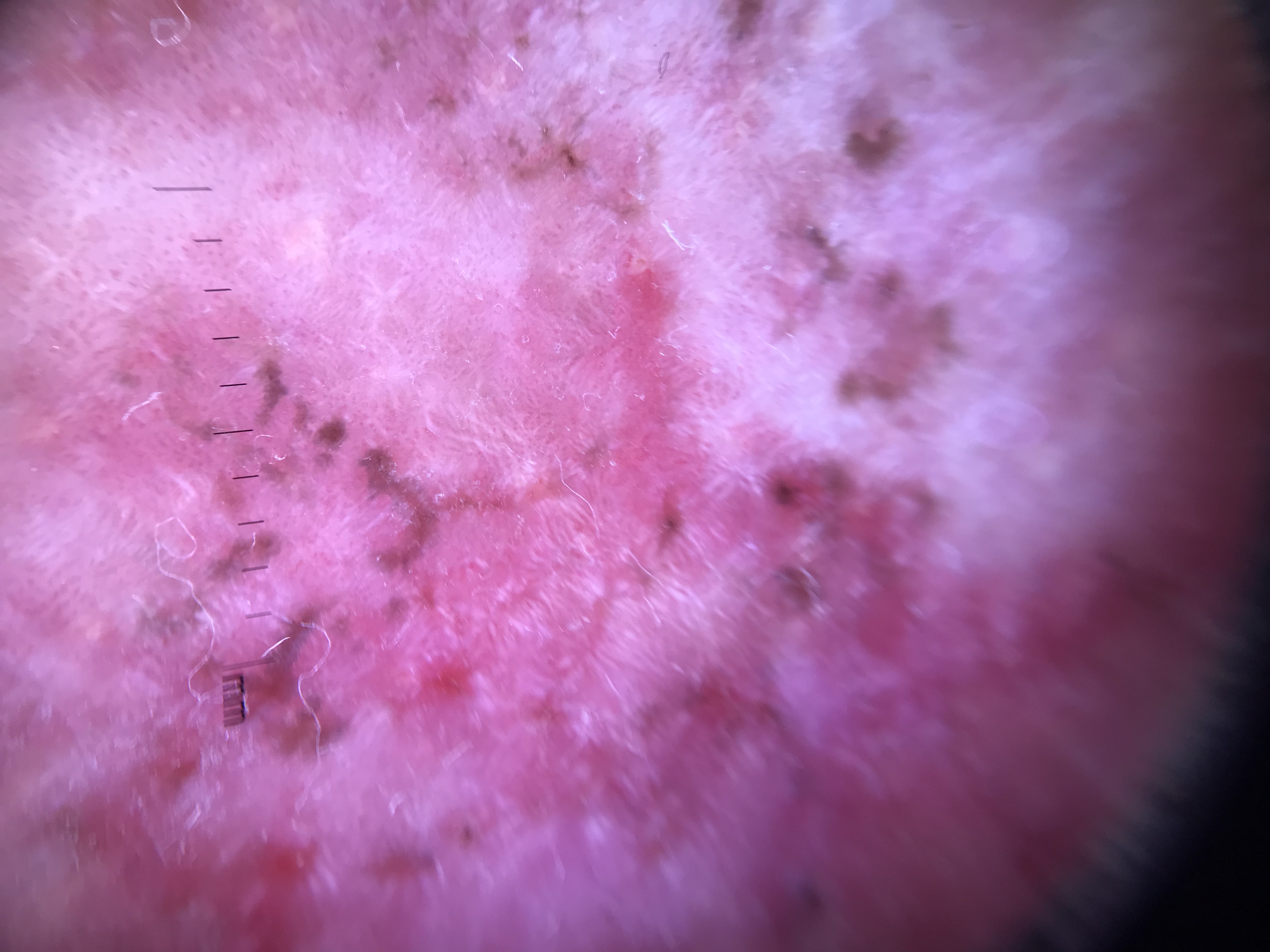– class · basal cell carcinoma (biopsy-proven)